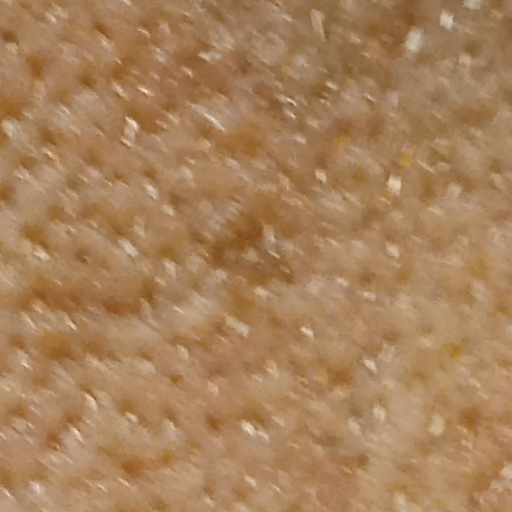Findings:
* referral: research study (no referral diagnosis)
* image: clinical photograph
* subject: male, 66 years of age
* risk factors: a prior organ transplant
* nevus count: few melanocytic nevi overall
* sun reaction: skin reddens with sun exposure
* location: the face
* size: 3 mm
* diagnosis: seborrheic keratosis (dermatologist consensus)